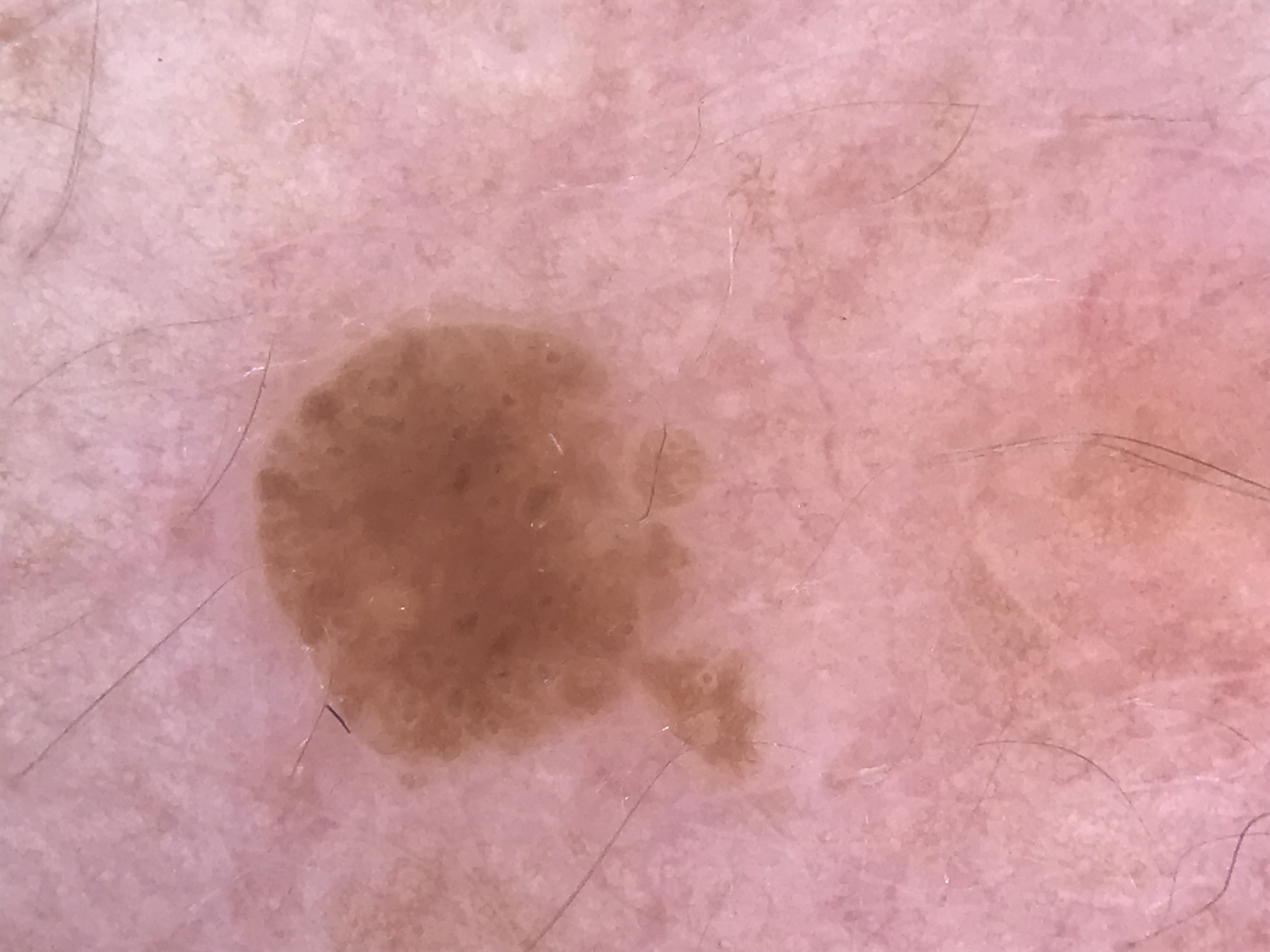| field | value |
|---|---|
| label | seborrheic keratosis (expert consensus) |